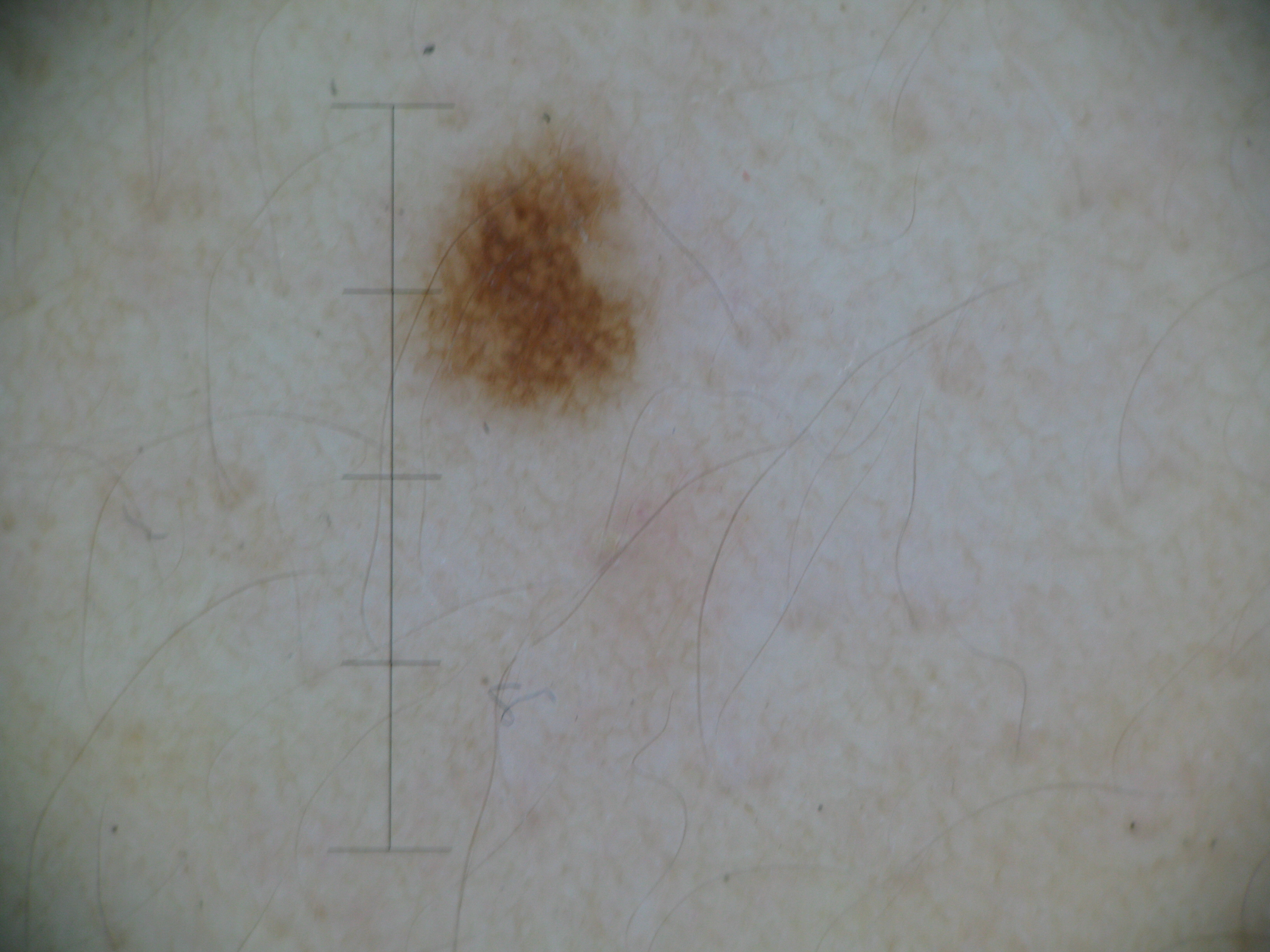A dermoscopic photograph of a skin lesion. The architecture is that of a banal lesion. The diagnostic label was a junctional nevus.